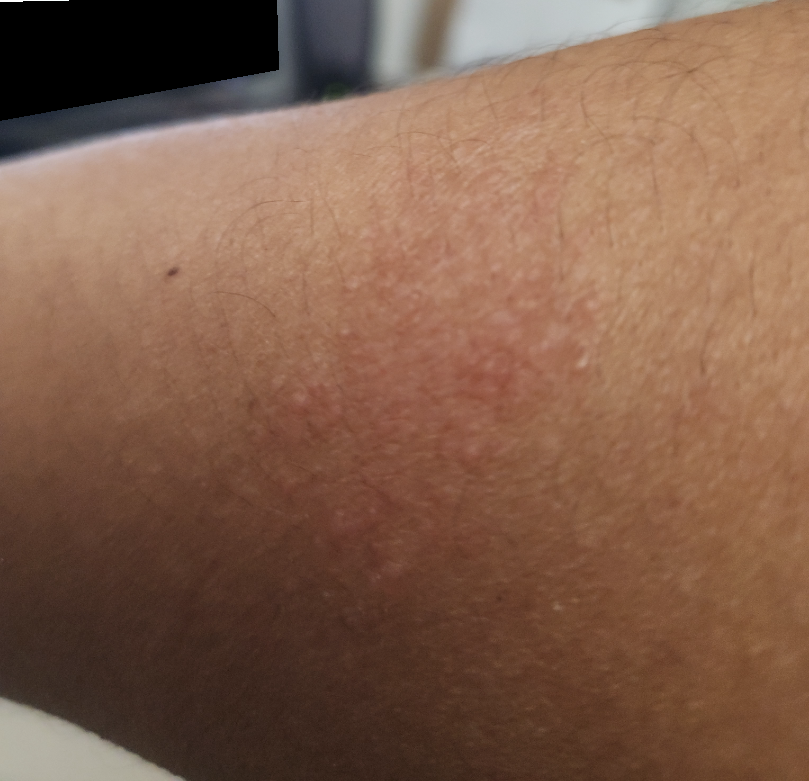The contributor notes the lesion is raised or bumpy and rough or flaky. The patient considered this skin that appeared healthy to them. The contributor notes the condition has been present for one to four weeks. Reported lesion symptoms include itching. Close-up view. The patient is female. The arm is involved. The reviewing panel's impression was: most likely Eczema; an alternative is Contact dermatitis; less probable is Tinea.